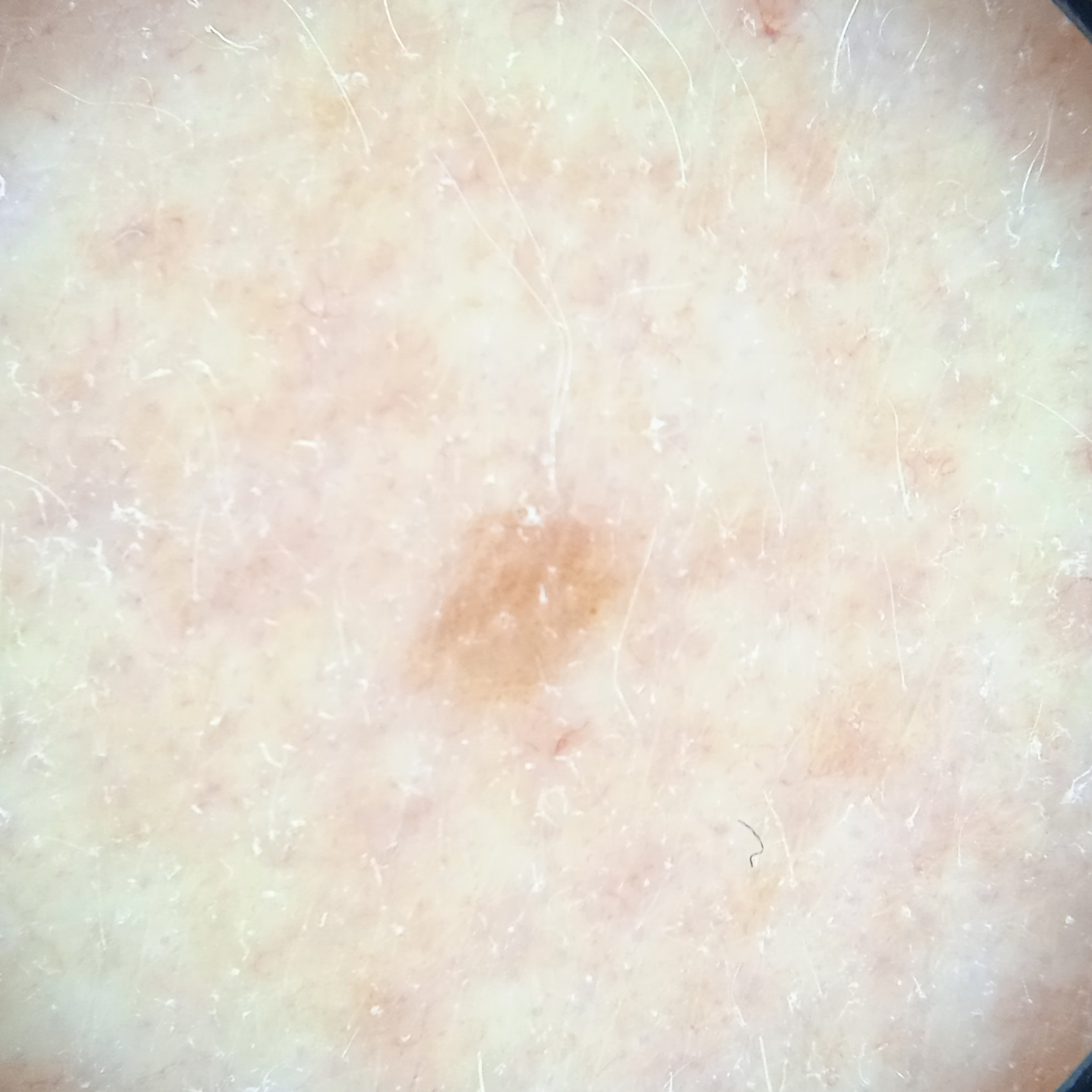referral: research study (no referral diagnosis)
subject: female, aged 92
image: dermoscopic image
diameter: 2.9 mm
diagnosis: melanocytic nevus (dermatologist consensus)